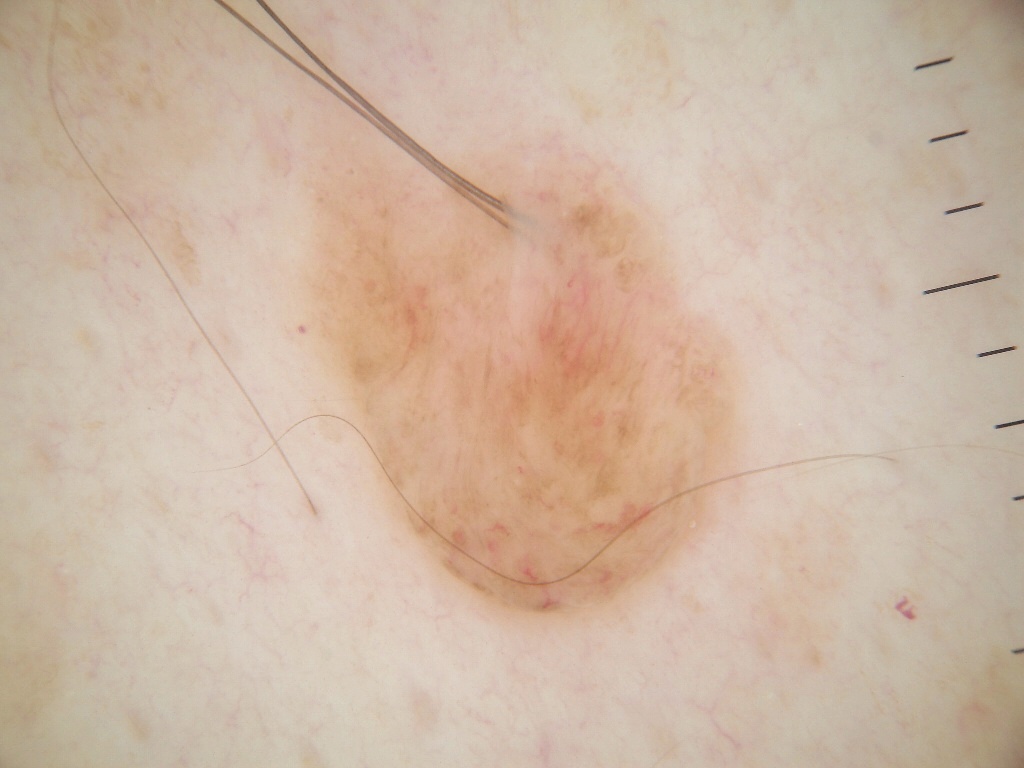The subject is a male about 60 years old.
A skin lesion imaged with a dermatoscope.
The lesion covers approximately 26% of the dermoscopic field.
With coordinates (x1, y1, x2, y2), the lesion is located at 265, 95, 770, 633.
Dermoscopic examination shows no streaks, pigment network, milia-like cysts, globules, or negative network.
Biopsy-confirmed as a melanoma.